A skin lesion imaged with a dermatoscope: 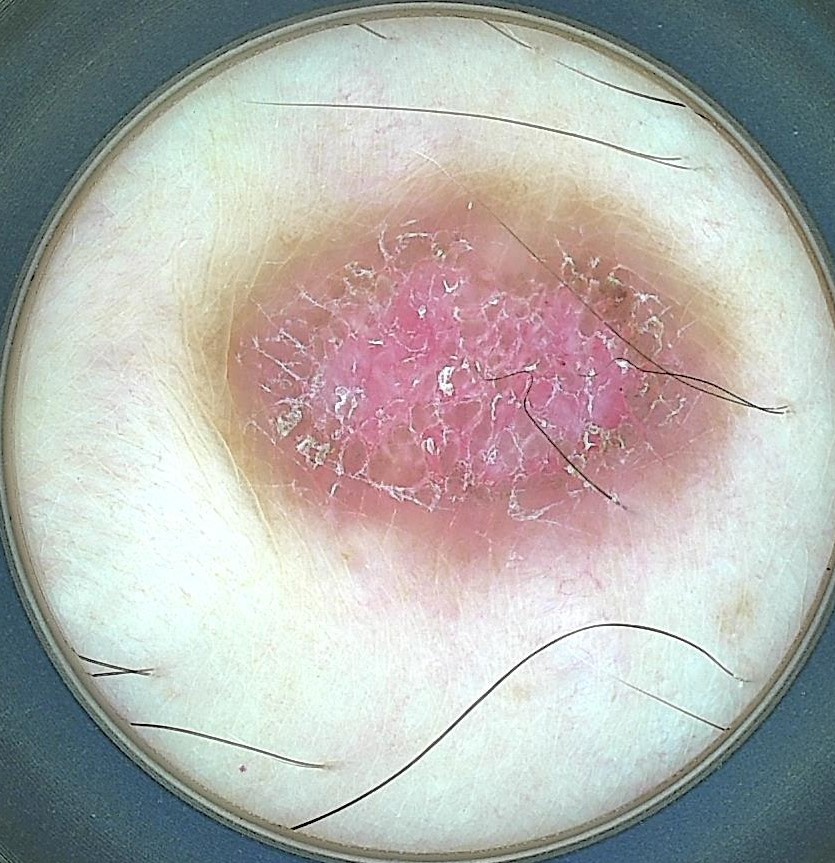classification: fibro-histiocytic, assessment: dermatofibroma (expert consensus).